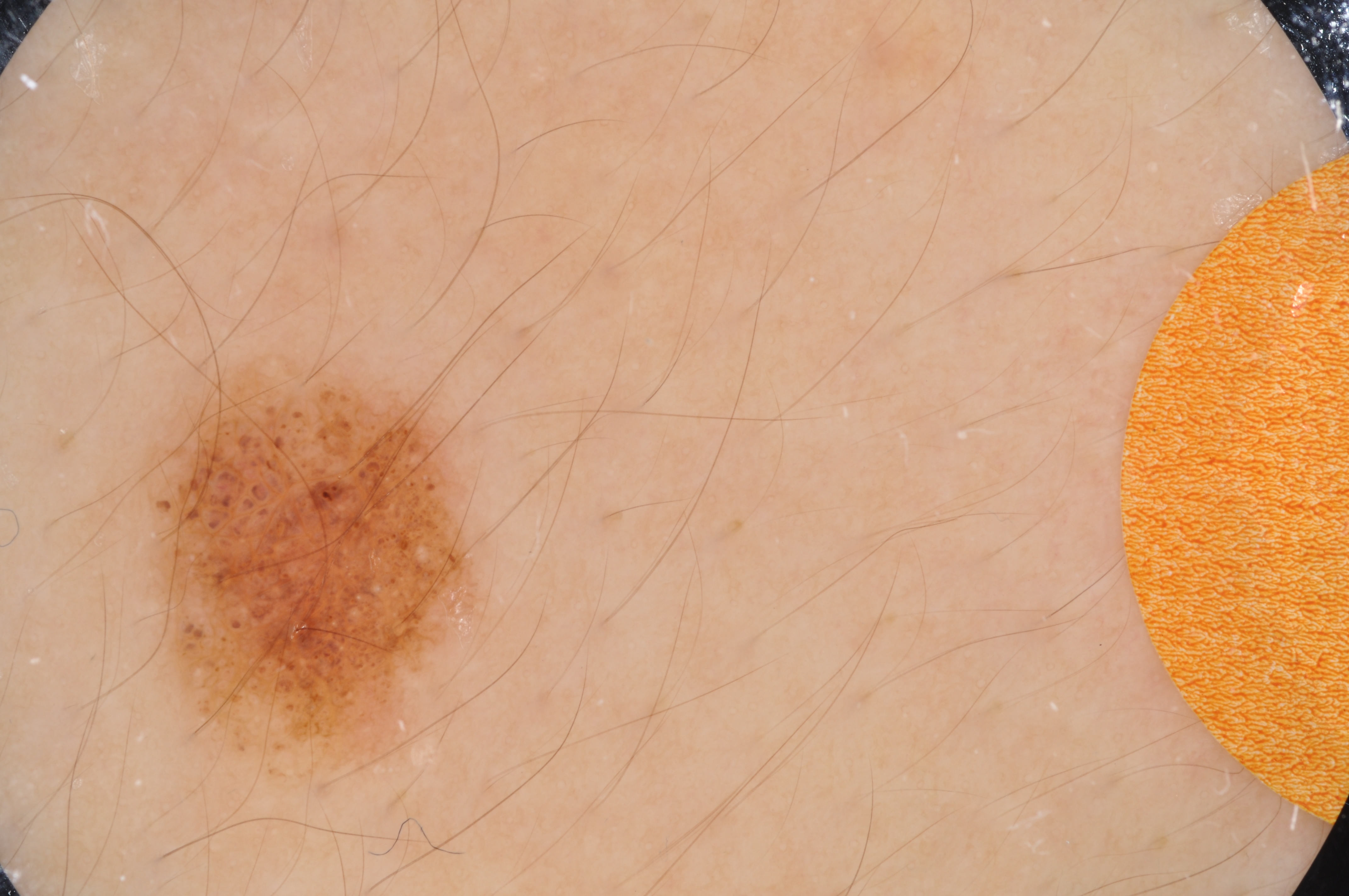| feature | finding |
|---|---|
| image type | dermatoscopic image of a skin lesion |
| bounding box | 136 351 490 783 |
| dermoscopic findings | milia-like cysts; absent: pigment network, negative network, globules, and streaks |
| assessment | a melanocytic nevus |